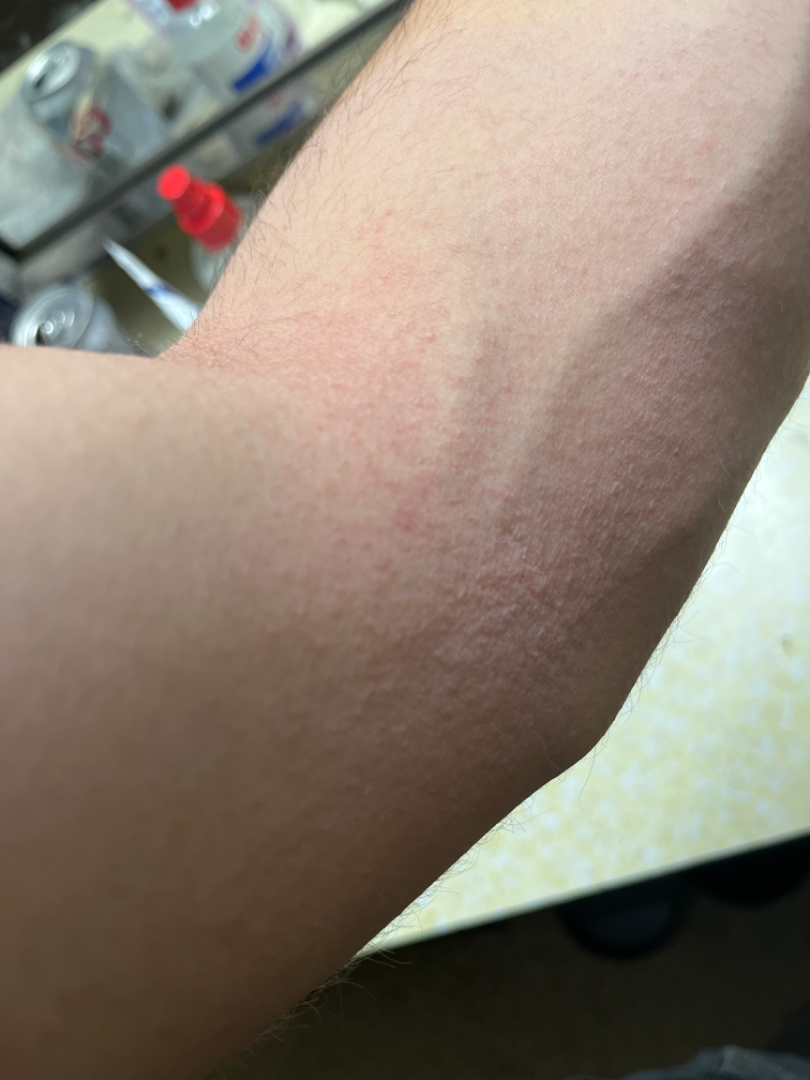Fitzpatrick III. A close-up photograph. On remote dermatologist review: Eczema (leading).